A clinical close-up photograph of a skin lesion. The chart records prior skin cancer (patient or family), no prior malignancy (patient or family), and no alcohol use. A female subject in their 60s. The patient was assessed as FST II:
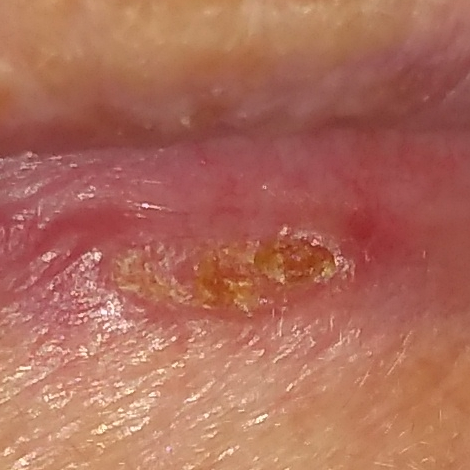Findings:
– region · a lip
– symptoms · no itching, no elevation
– pathology · nevus (biopsy-proven)